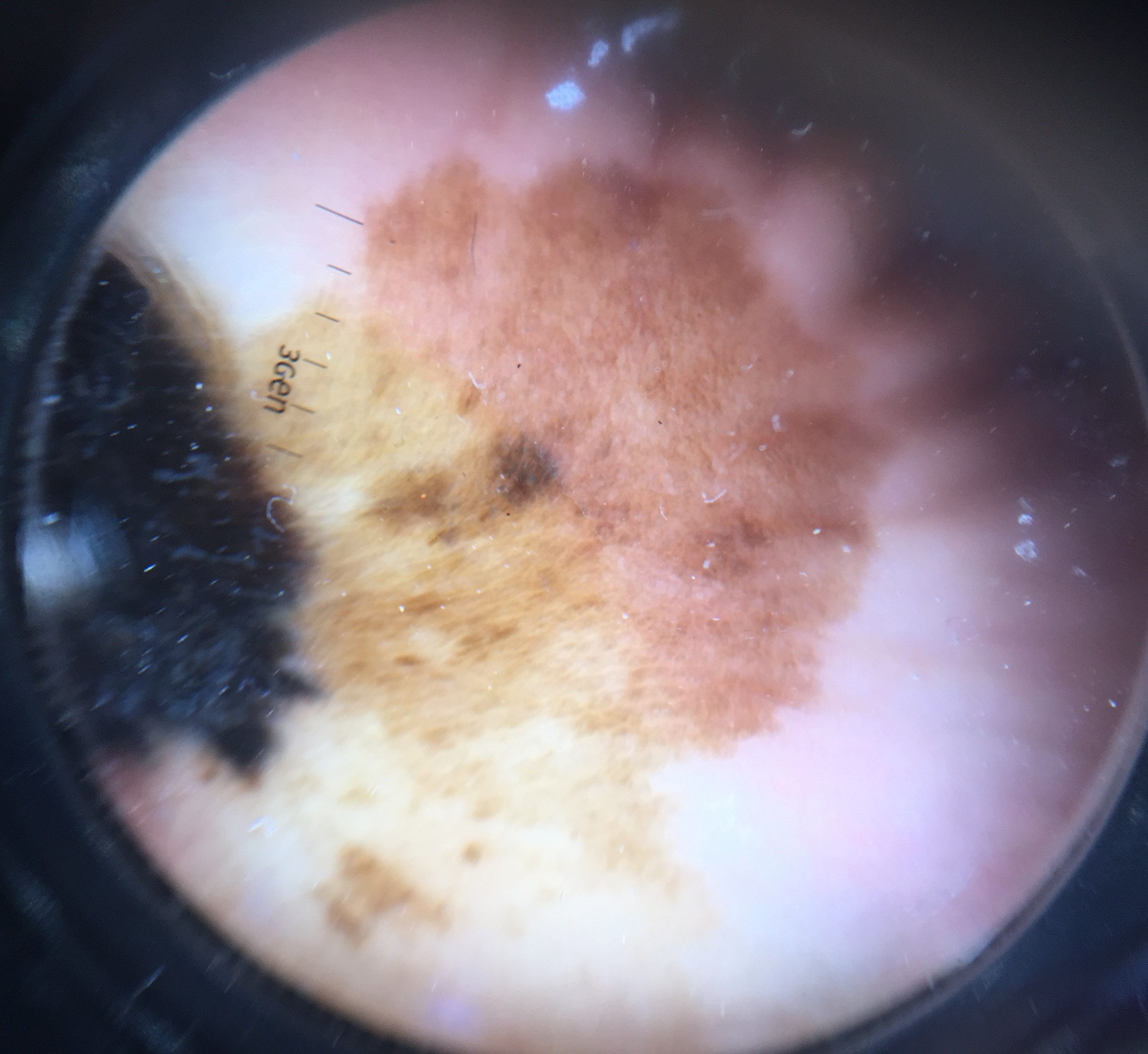A dermoscopic image of a skin lesion. Biopsy-confirmed as a malignancy — an acral lentiginous melanoma.